The affected area is the leg; the subject is a female aged 40–49; this image was taken at a distance:
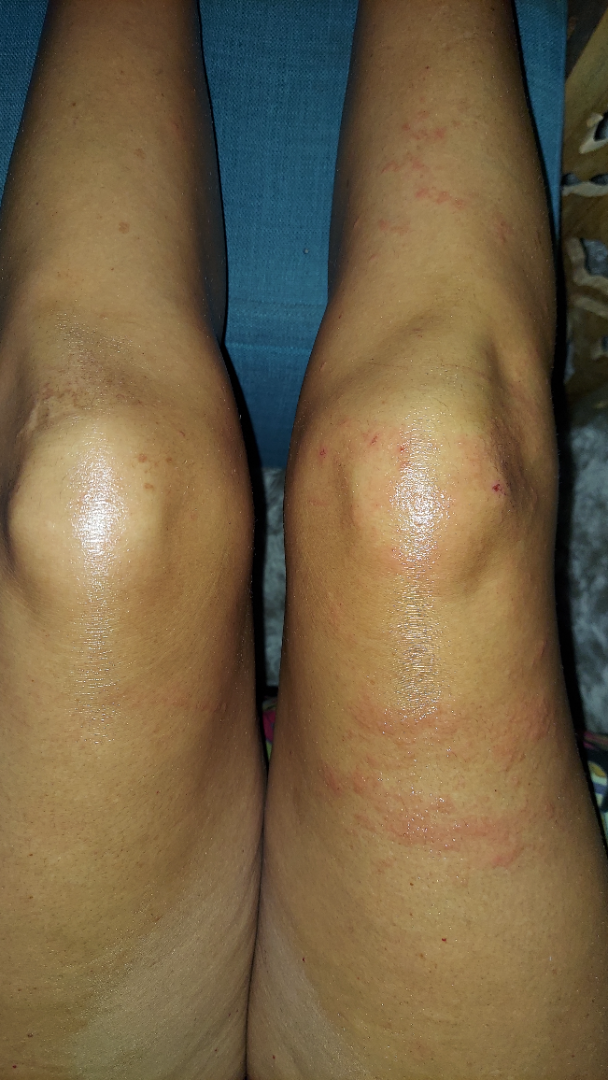Three dermatologists independently reviewed the case: most consistent with Allergic Contact Dermatitis; less probable is Phytophotodermatitis; lower on the differential is Herpes Zoster; less likely is Urticaria; a more distant consideration is Insect Bite.